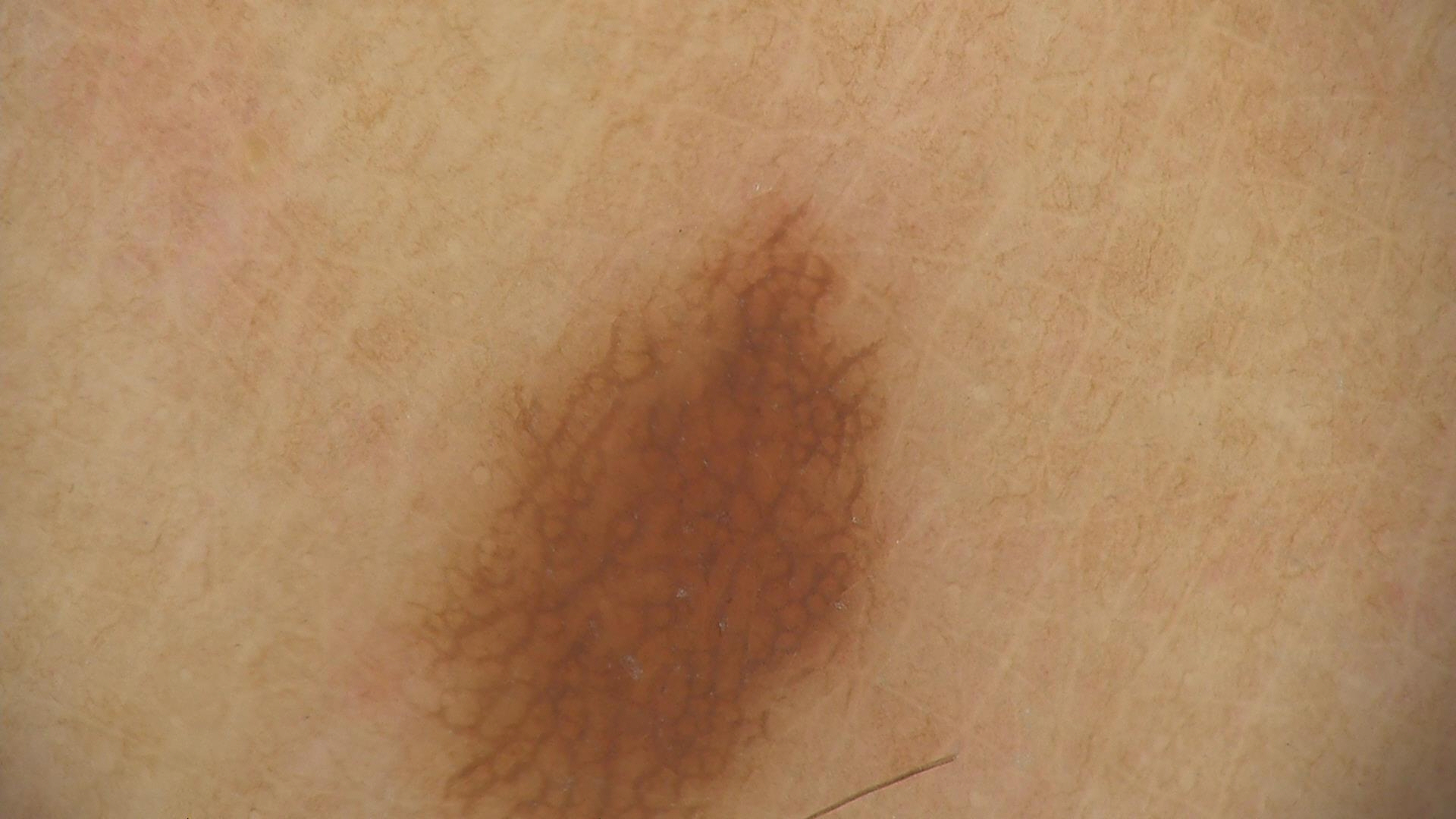Impression: Diagnosed as a junctional nevus.